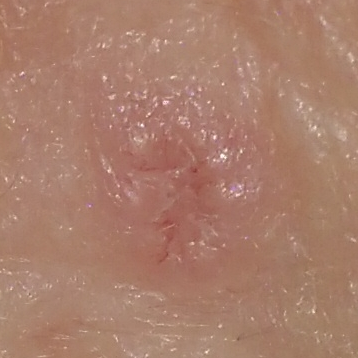exposures: prior malignancy (patient or family), no alcohol use | image: smartphone clinical photo | location: the face | diameter: 4 × 3 mm | patient-reported symptoms: elevation / no itching | diagnostic label: basal cell carcinoma (biopsy-proven).